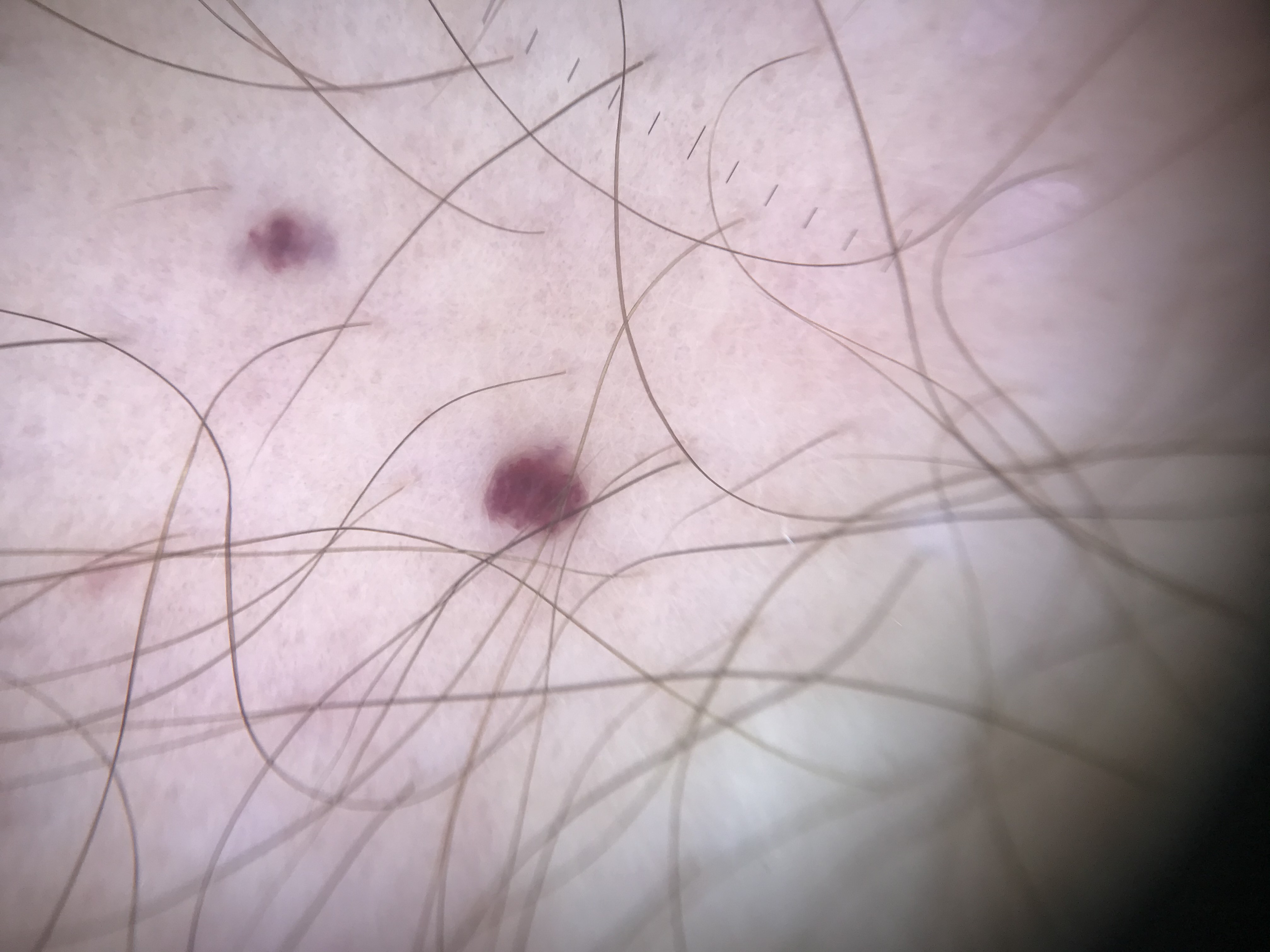{"image": "dermoscopy", "lesion_type": {"main_class": "vascular"}, "diagnosis": {"name": "hemangioma", "code": "ha", "malignancy": "benign", "super_class": "non-melanocytic", "confirmation": "expert consensus"}}